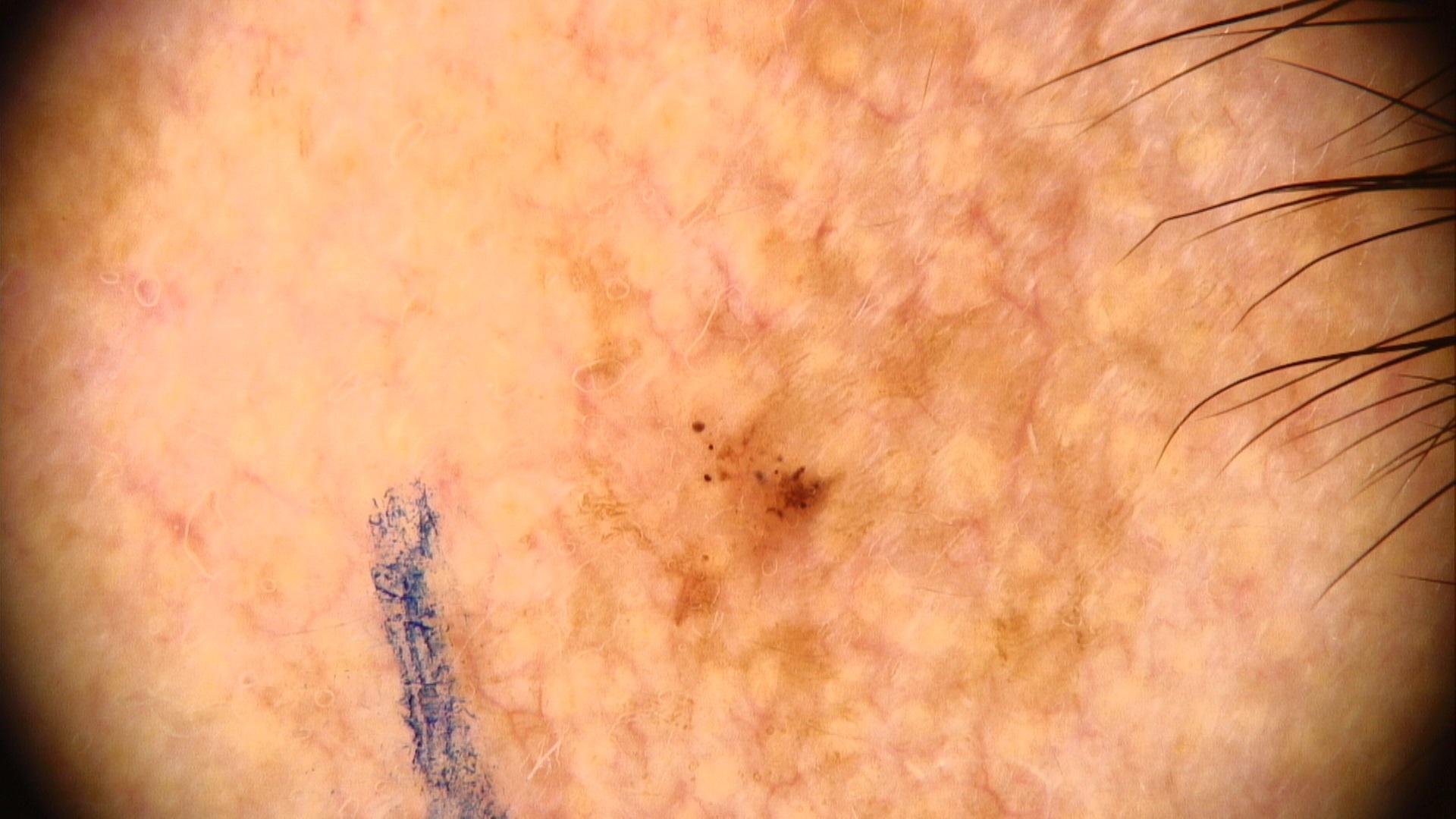The chart documents no previous melanoma and no first-degree relative with melanoma. A female patient aged 48-52. The lesion is on the head or neck. Biopsy-confirmed as a malignancy — a basal cell carcinoma.